A dermoscopy image of a single skin lesion.
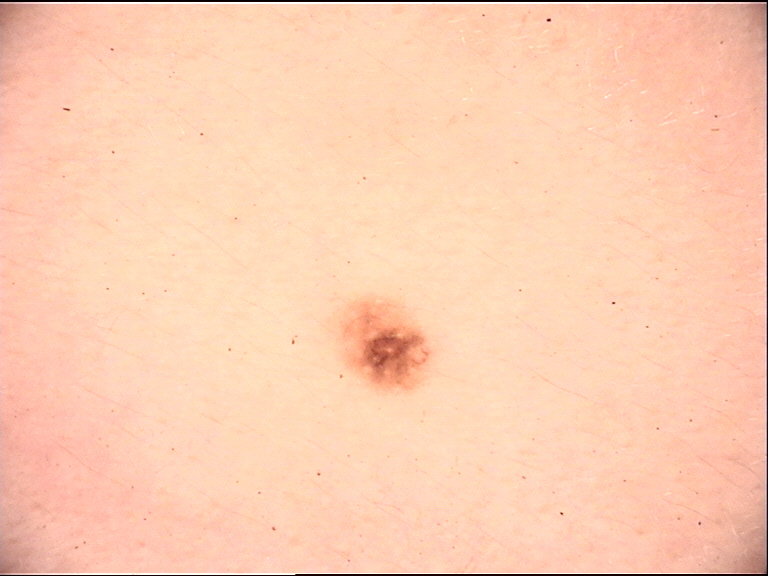The architecture is that of a compound, banal lesion. Classified as a Miescher nevus.